Present for one to four weeks; the patient also reports joint pain and fatigue; close-up view; the lesion is described as rough or flaky, raised or bumpy and fluid-filled; self-categorized by the patient as a rash; the contributor is 40–49, female; the head or neck and front of the torso are involved; the lesion is associated with itching, enlargement and bothersome appearance — 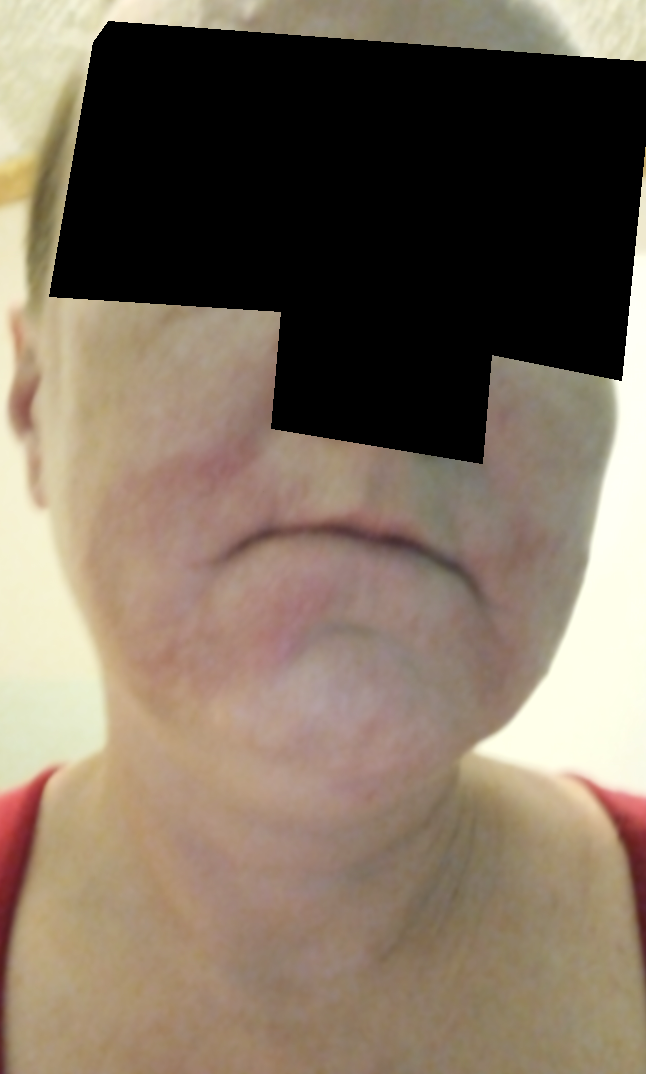<case>
<assessment>not assessable</assessment>
</case>